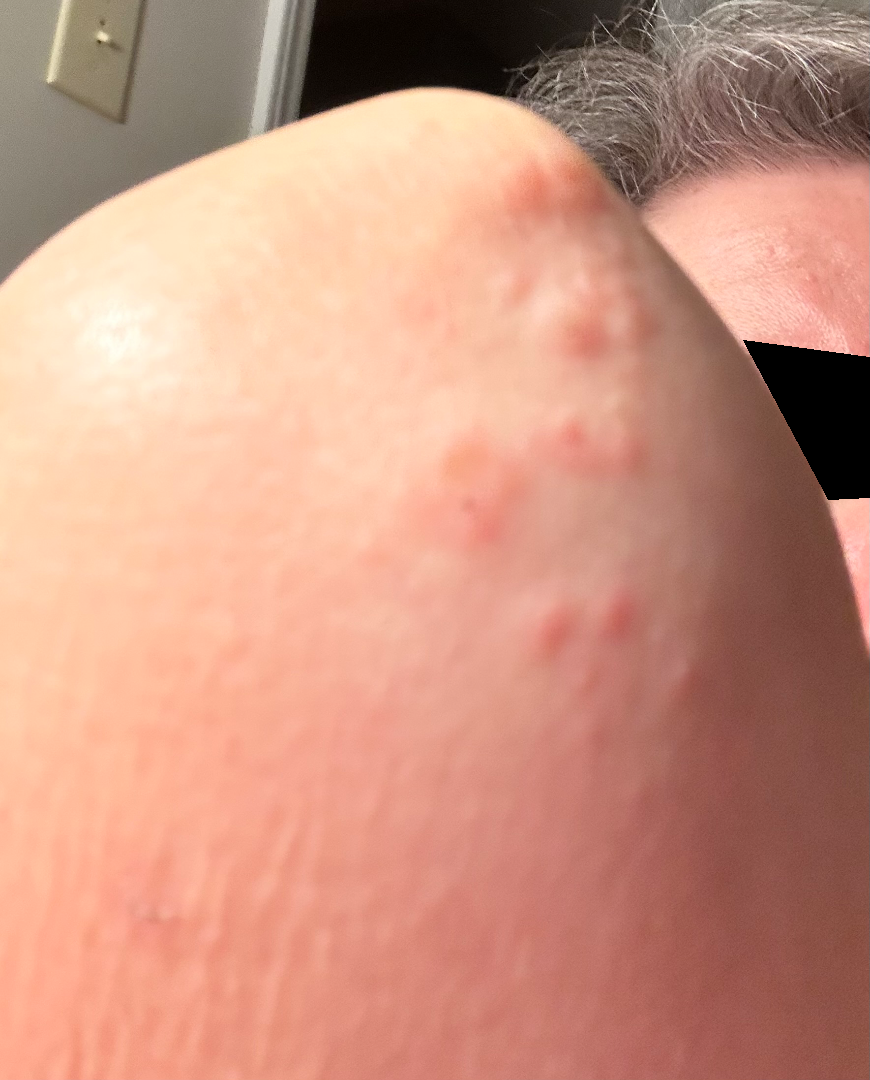The case was difficult to assess from the available photograph.
Female contributor, age 50–59.
The patient considered this a rash.
The patient reported no systemic symptoms.
This is a close-up image.
The lesion involves the arm.
The contributor notes itching.